The leg is involved · the photograph is a close-up of the affected area.
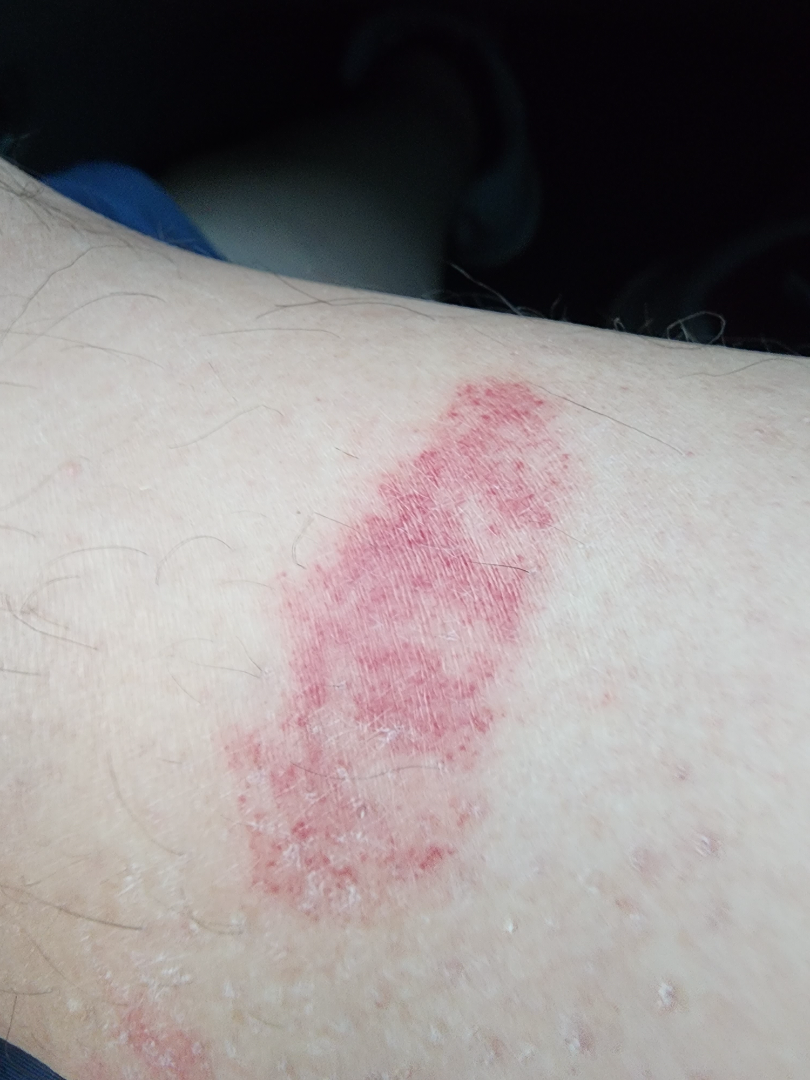Q: What is the dermatologist's impression?
A: reviewed remotely by one dermatologist: consistent with Purpura